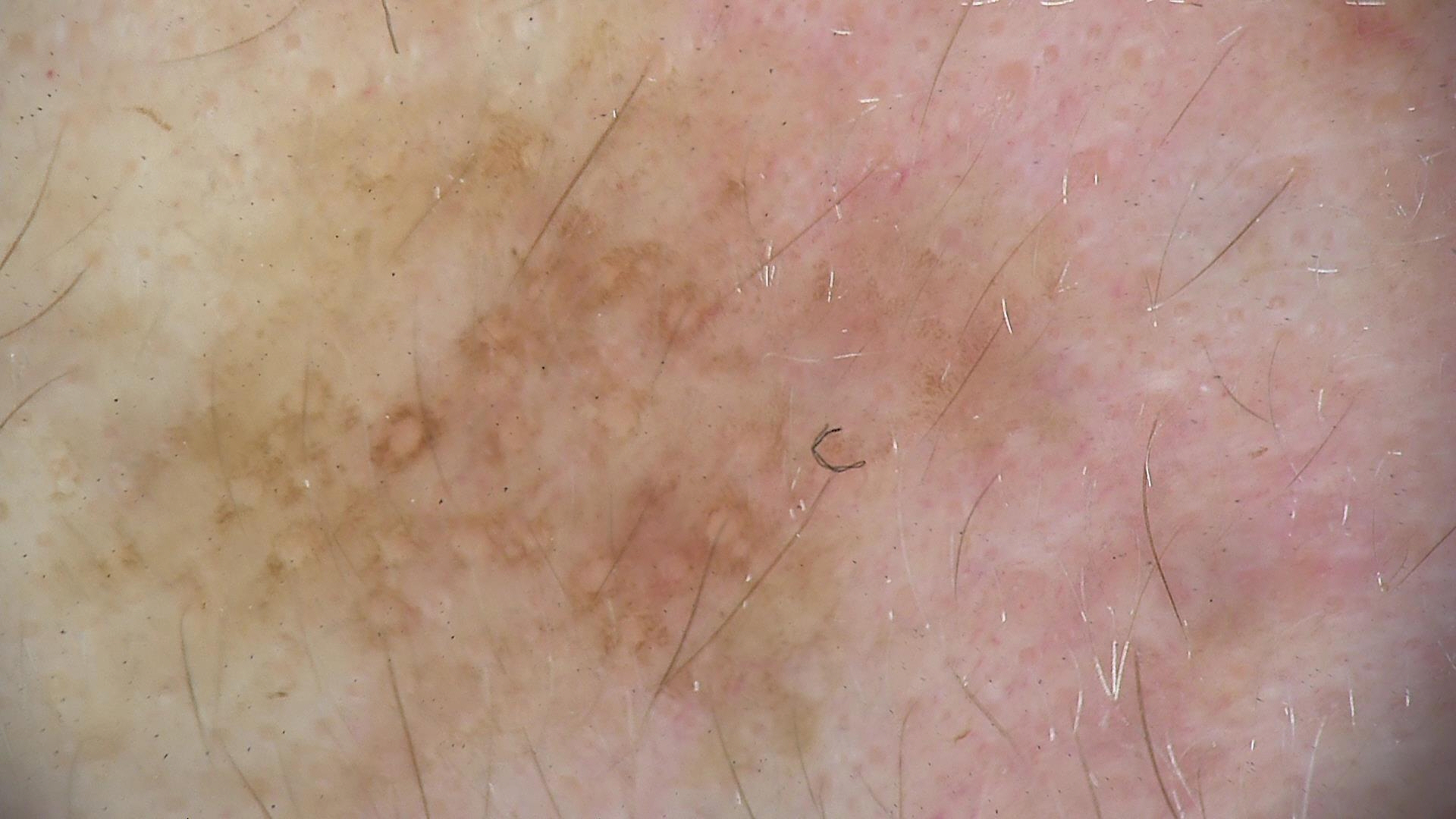diagnosis — seborrheic keratosis (expert consensus).